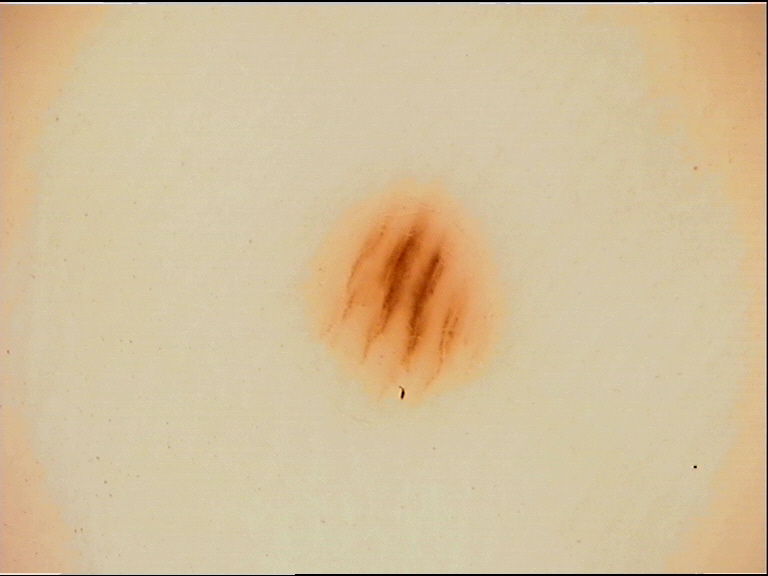Q: What kind of image is this?
A: dermatoscopy
Q: How is the lesion classified?
A: banal
Q: What is the diagnosis?
A: acral junctional nevus (expert consensus)